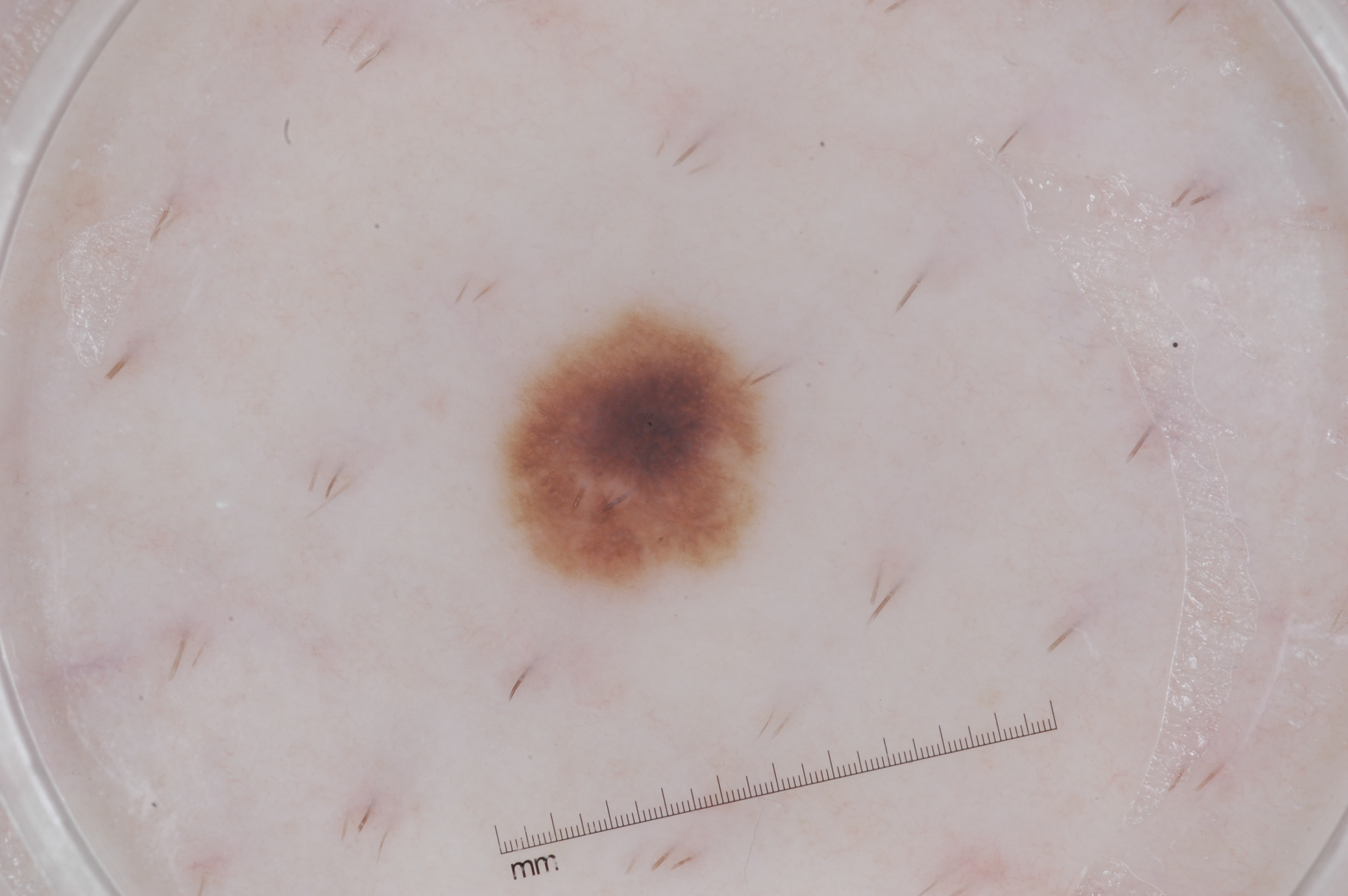Notes:
- modality — dermoscopy of a skin lesion
- lesion size — ~5% of the field
- bounding box — <box>491, 294, 790, 604</box>
- features — milia-like cysts and pigment network
- diagnostic label — a melanocytic nevus, a benign lesion